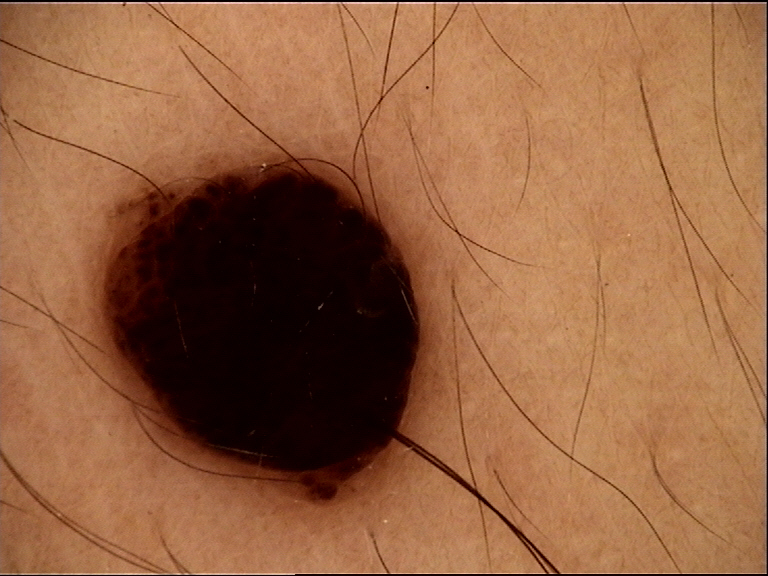  image: dermatoscopy
  lesion_type:
    main_class: banal
    pattern: dermal
  diagnosis:
    name: dermal nevus
    code: db
    malignancy: benign
    super_class: melanocytic
    confirmation: expert consensus